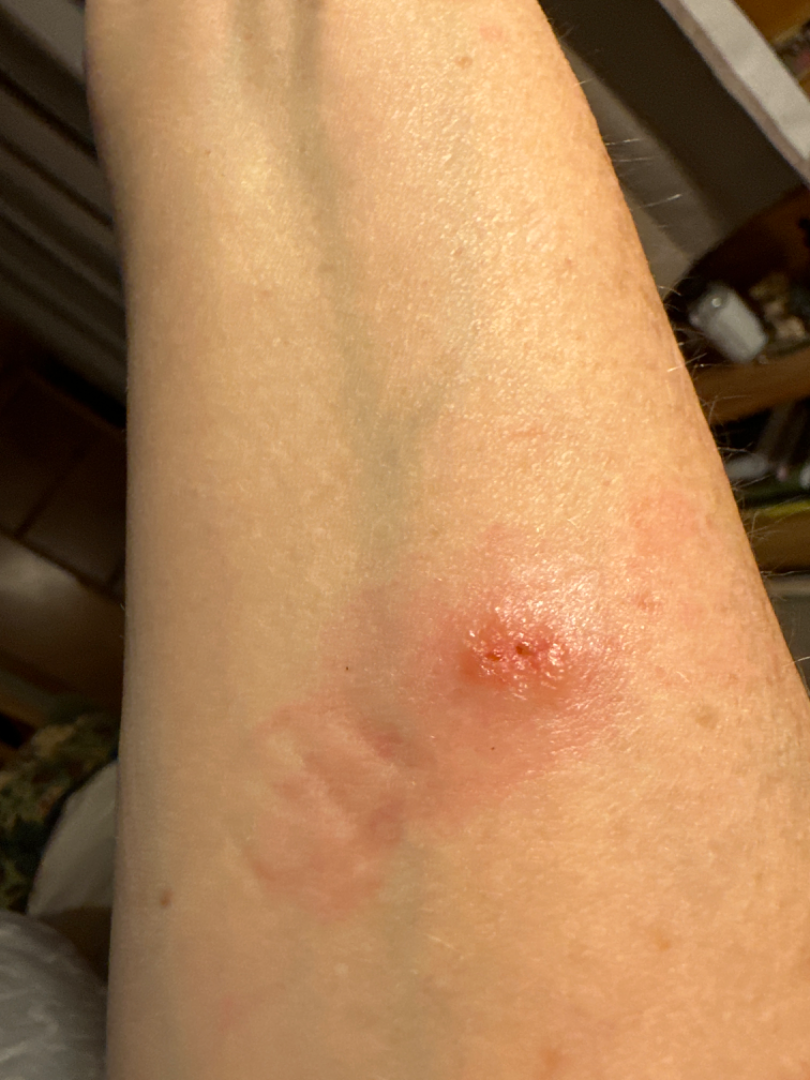differential diagnosis — Skin infection and Insect Bite were considered with similar weight; a remote consideration is Allergic Contact Dermatitis.